The subject is a female aged 18–29 · close-up view · the head or neck is involved: 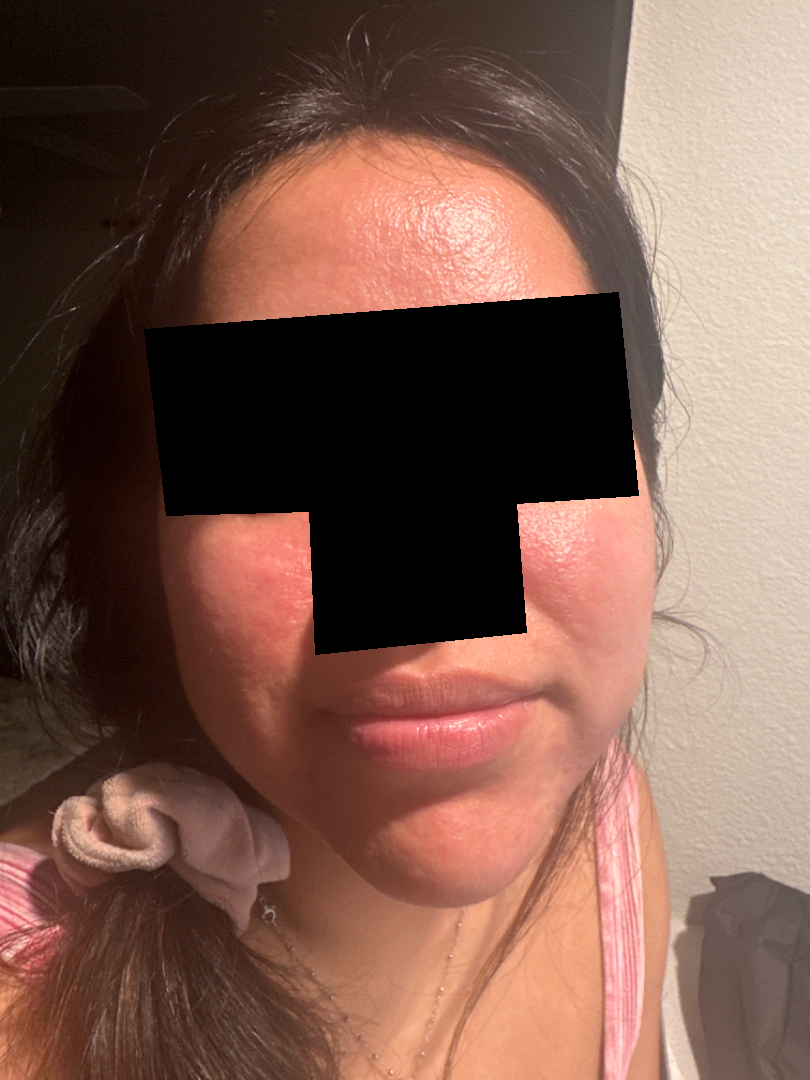Texture is reported as raised or bumpy.
Fitzpatrick skin type III; non-clinician graders estimated MST 2 or 4.
The patient described the issue as a rash.
Reported duration is about one day.
Reported lesion symptoms include itching.
Reviewed remotely by three dermatologists: in keeping with Rosacea.